Skin tone: Fitzpatrick IV; the photo was captured at a distance; the patient indicates the lesion is raised or bumpy; the lesion involves the arm; reported duration is one to four weeks — 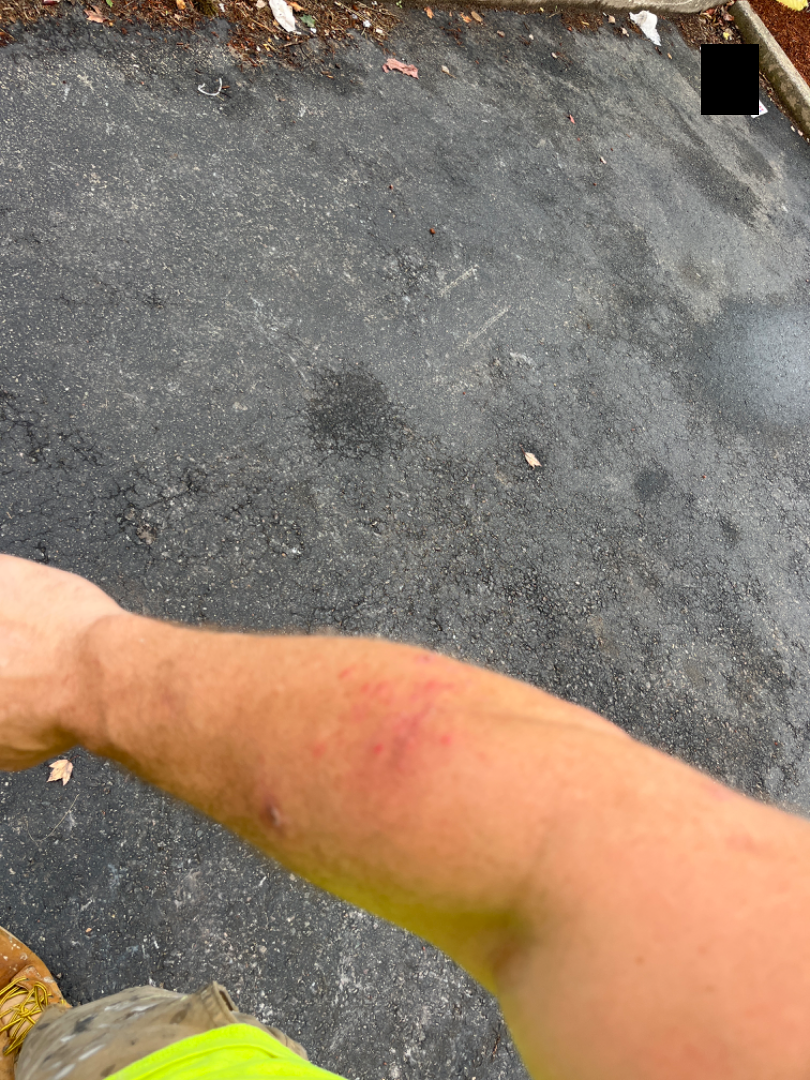assessment = one reviewing dermatologist: most consistent with Folliculitis; also consider Dermatitis herpetiformis; possibly Acute and chronic dermatitis.